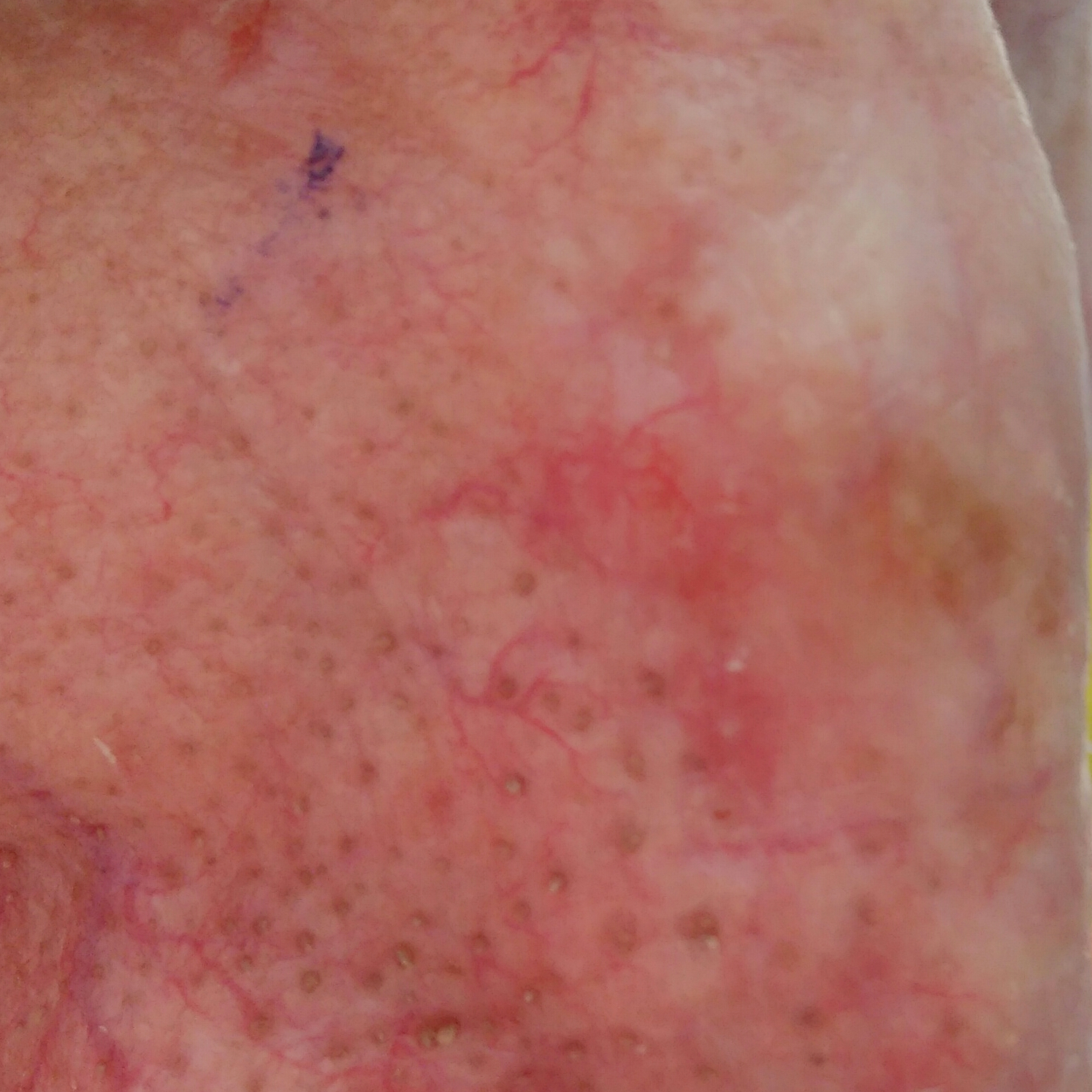subject = male, 73 years old
anatomic site = the nose
symptoms = no itching
pathology = basal cell carcinoma (biopsy-proven)